The photograph is a close-up of the affected area: 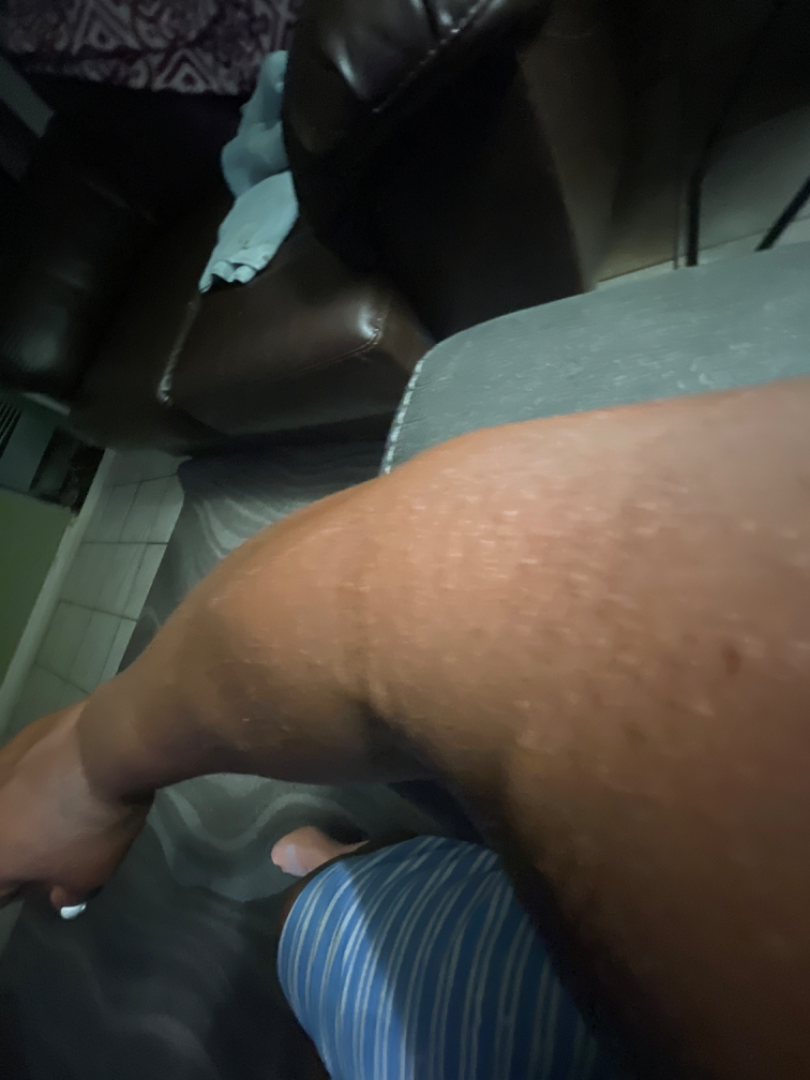The reviewer was unable to grade this case for skin condition.